The patient describes having numerous moles. A dermoscopy image of a skin lesion. The patient says their skin reddens with sun exposure: 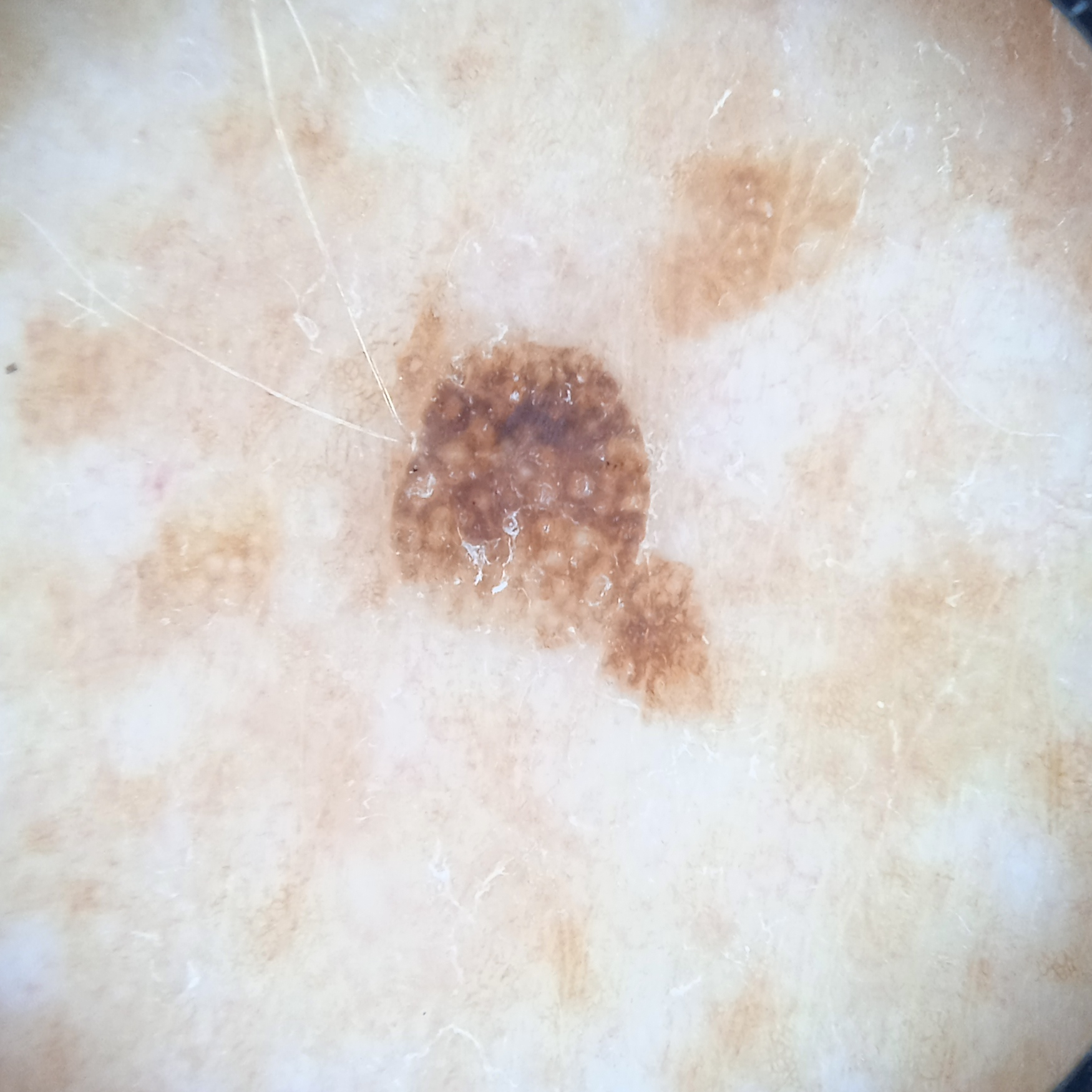{"lesion_location": "the back", "lesion_size": {"diameter_mm": 5.5}, "diagnosis": {"name": "seborrheic keratosis", "malignancy": "benign"}}